The subject is male · close-up view · the affected area is the arm and leg: 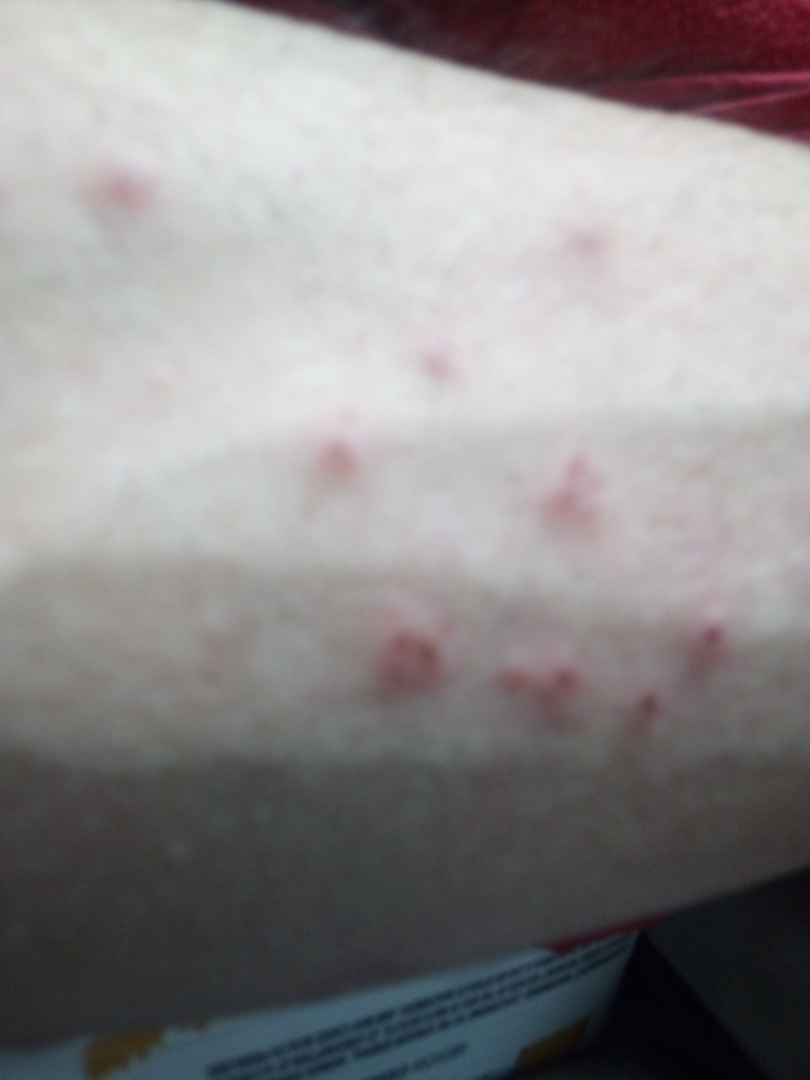The image was not sufficient for the reviewer to characterize the skin condition.
The patient considered this a rash.
Skin tone: Fitzpatrick skin type III; human graders estimated a Monk Skin Tone of 1.
Symptoms reported: bothersome appearance, itching and enlargement.
The patient also reports fatigue.
Present for less than one week.